Dermoscopy of a skin lesion:
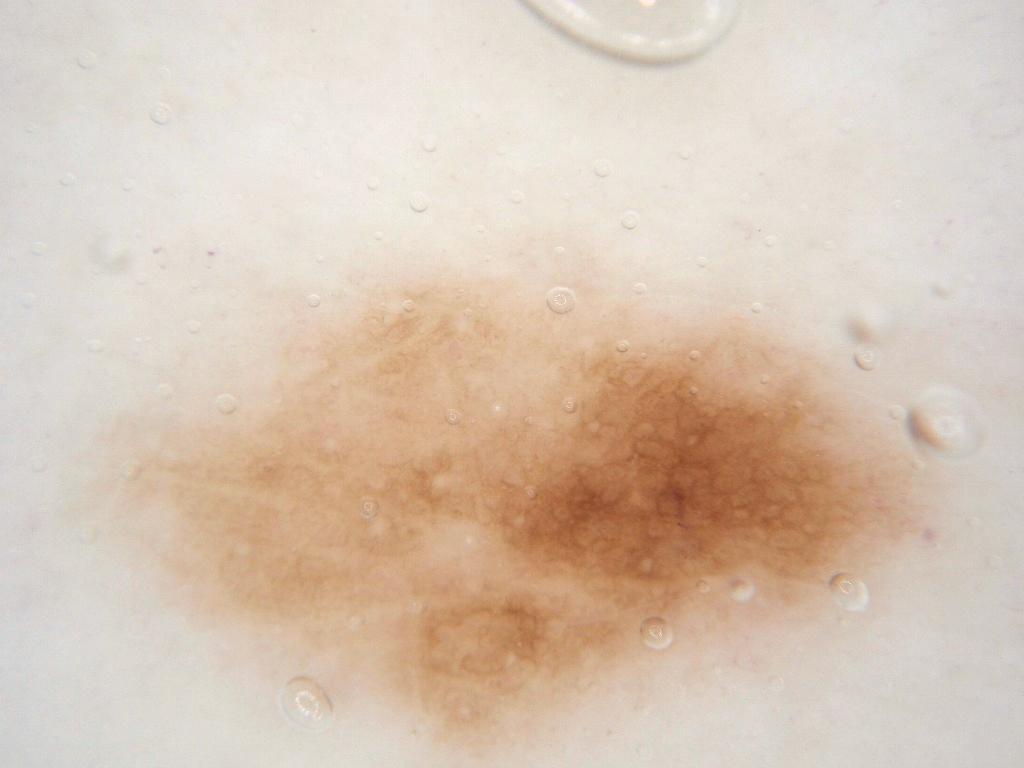location: [51, 221, 965, 764]; impression: a benign lesion.